Imaged for a research study, with no referral diagnosis recorded. A male subject 72 years of age. The patient describes having few moles overall.
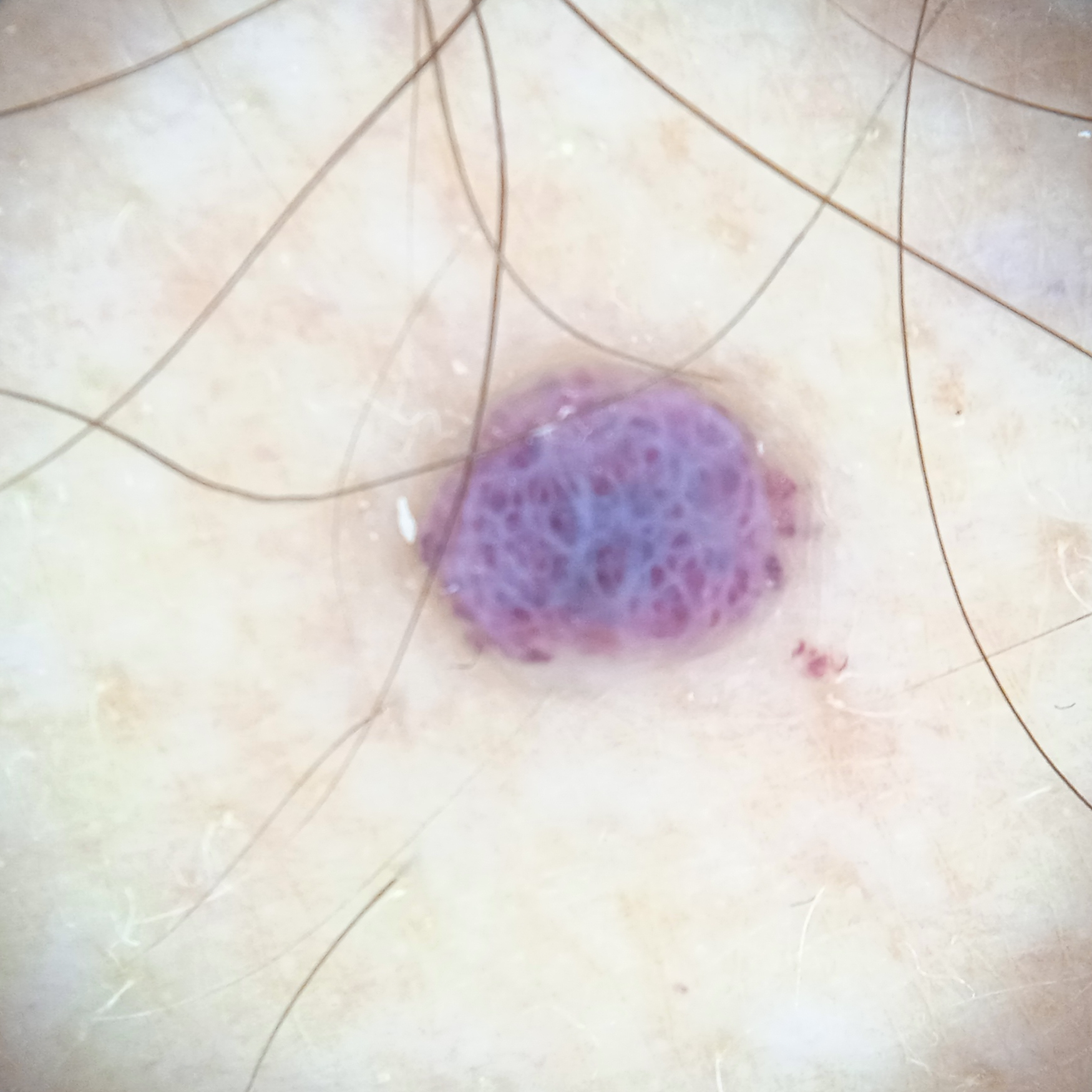The lesion involves the torso. The consensus diagnosis for this lesion was an angioma.